Per the chart, a previous melanoma but no melanoma in first-degree relatives · a skin lesion imaged with contact-polarized dermoscopy.
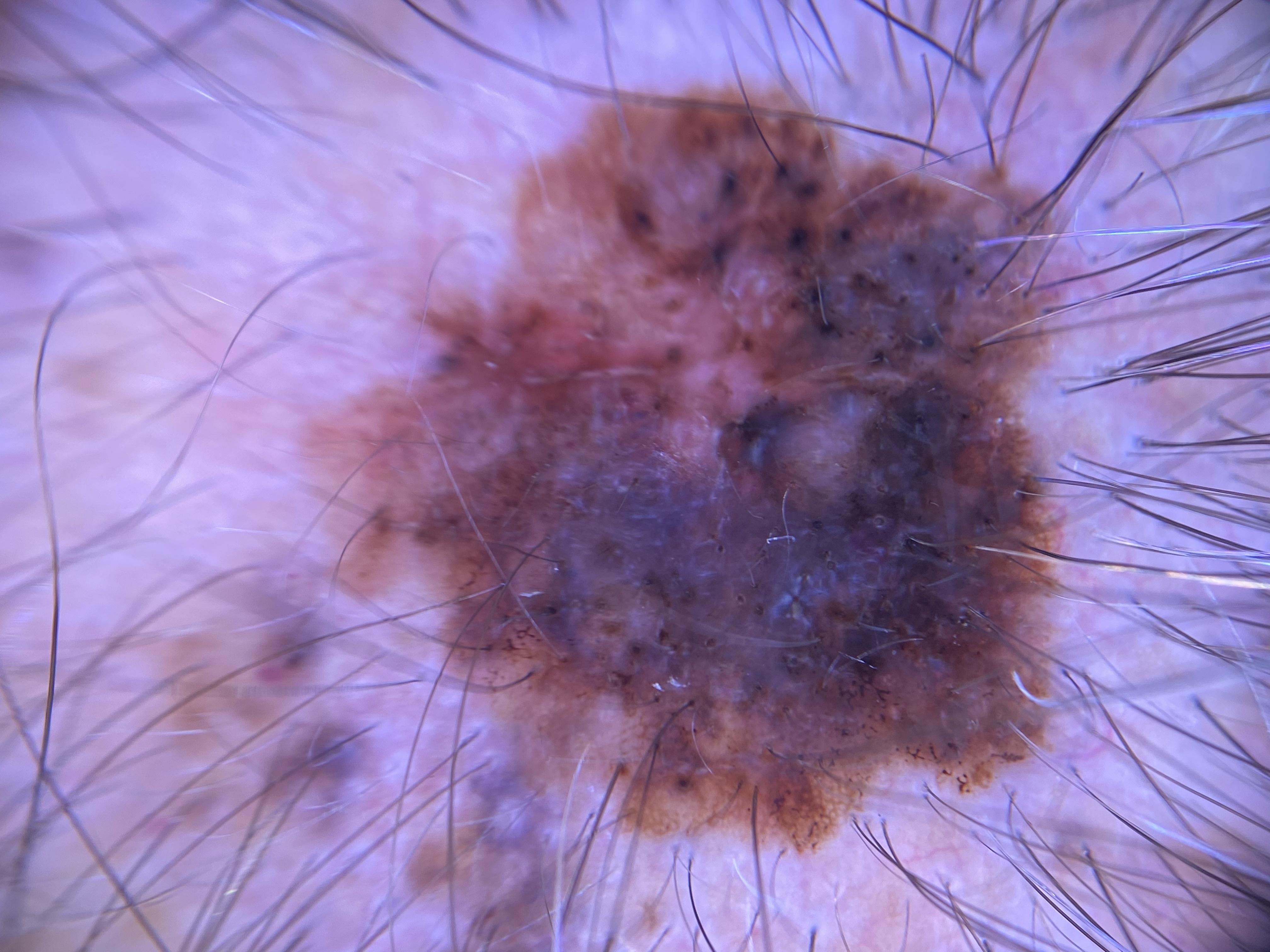anatomic site = the head or neck, diagnostic label = Melanoma (biopsy-proven).